A dermoscopic image of a skin lesion:
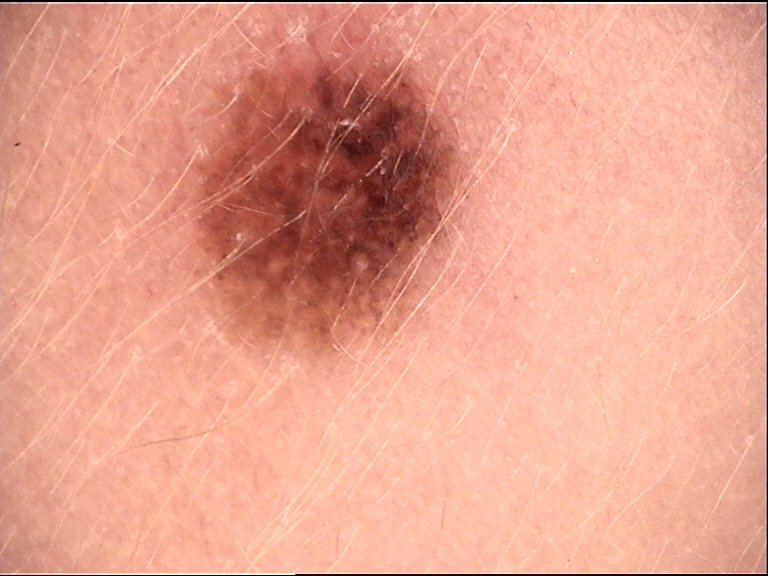Classified as a benign lesion — a dysplastic junctional nevus.